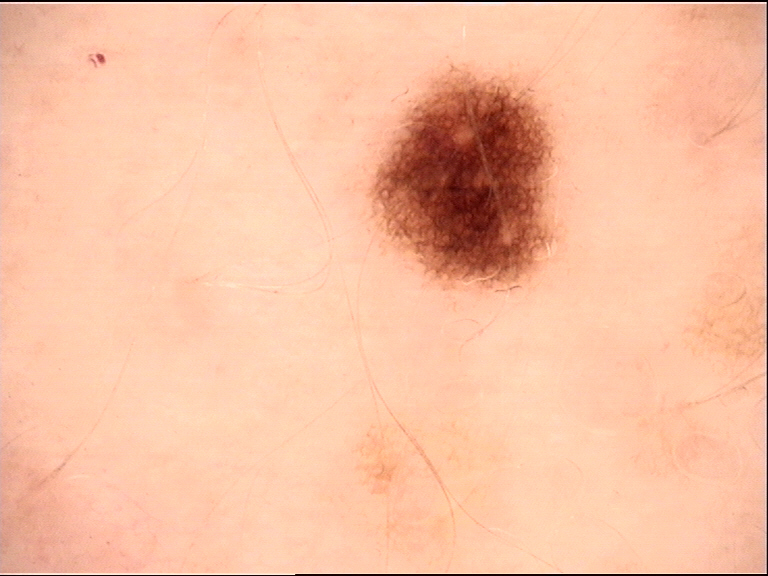imaging=dermoscopy
diagnosis=dysplastic junctional nevus (expert consensus)